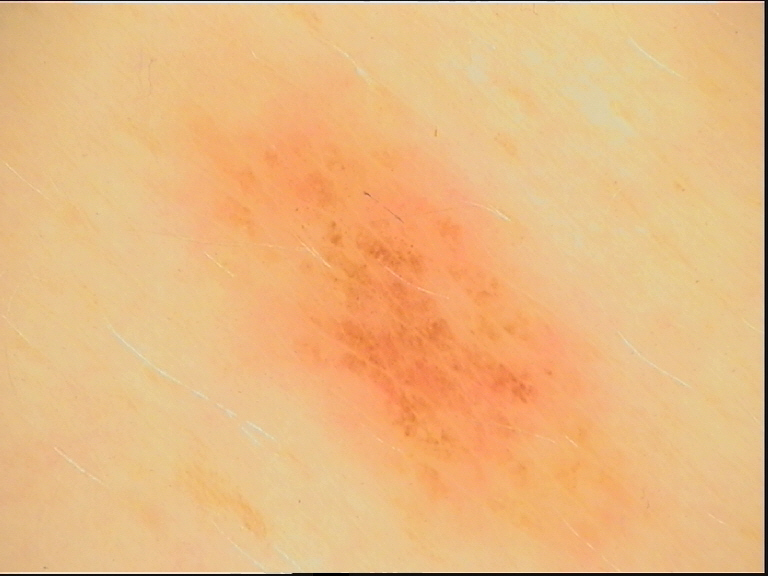Q: What is the diagnosis?
A: dysplastic junctional nevus (expert consensus)